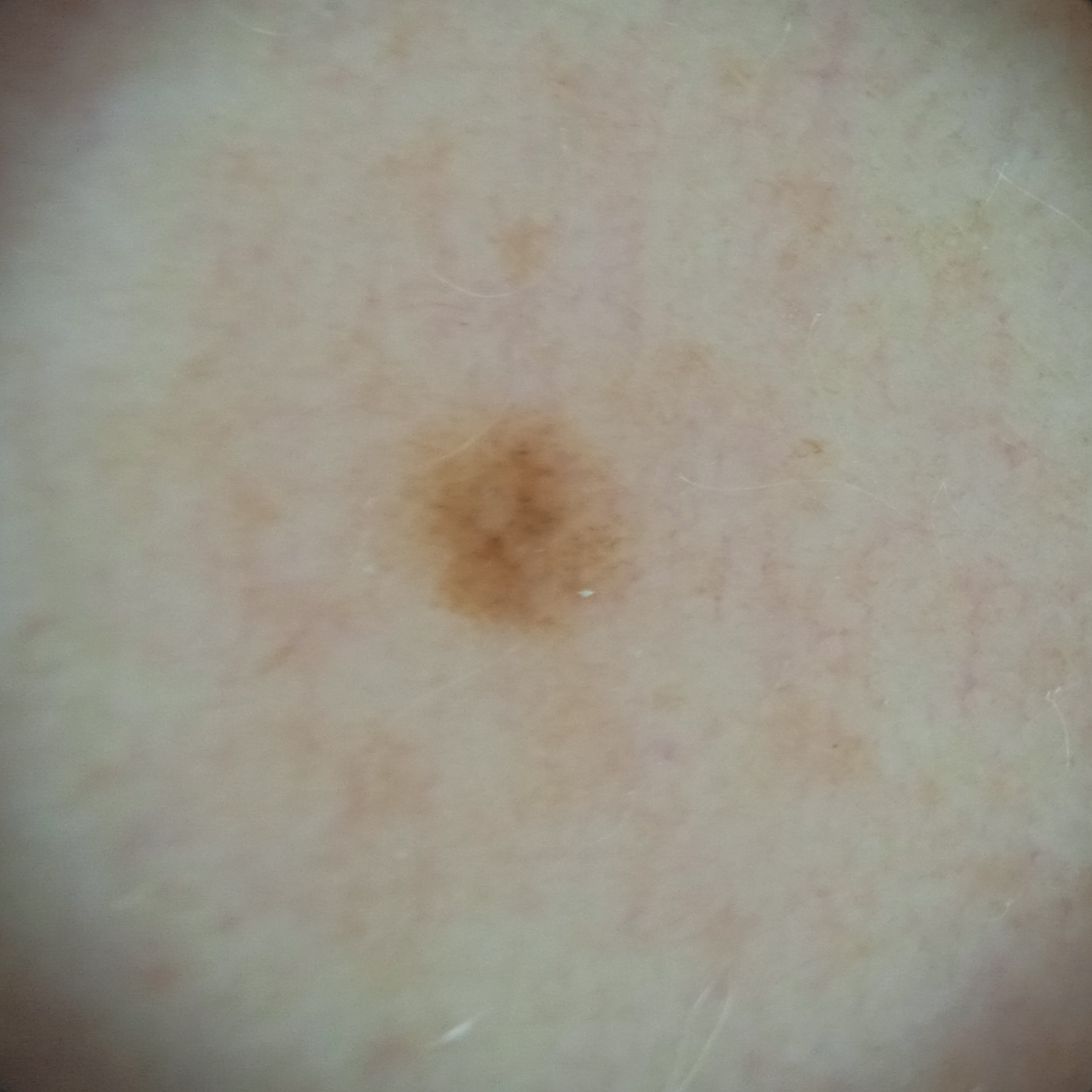Clinical context: A female subject aged 48. The patient reports a family history of skin cancer and a history of sunbed use. The patient says their skin reddens painfully with sun exposure. A skin lesion imaged with a dermatoscope. Located on an arm. The lesion is about 2.7 mm across. Conclusion: The consensus diagnosis for this lesion was a melanocytic nevus.